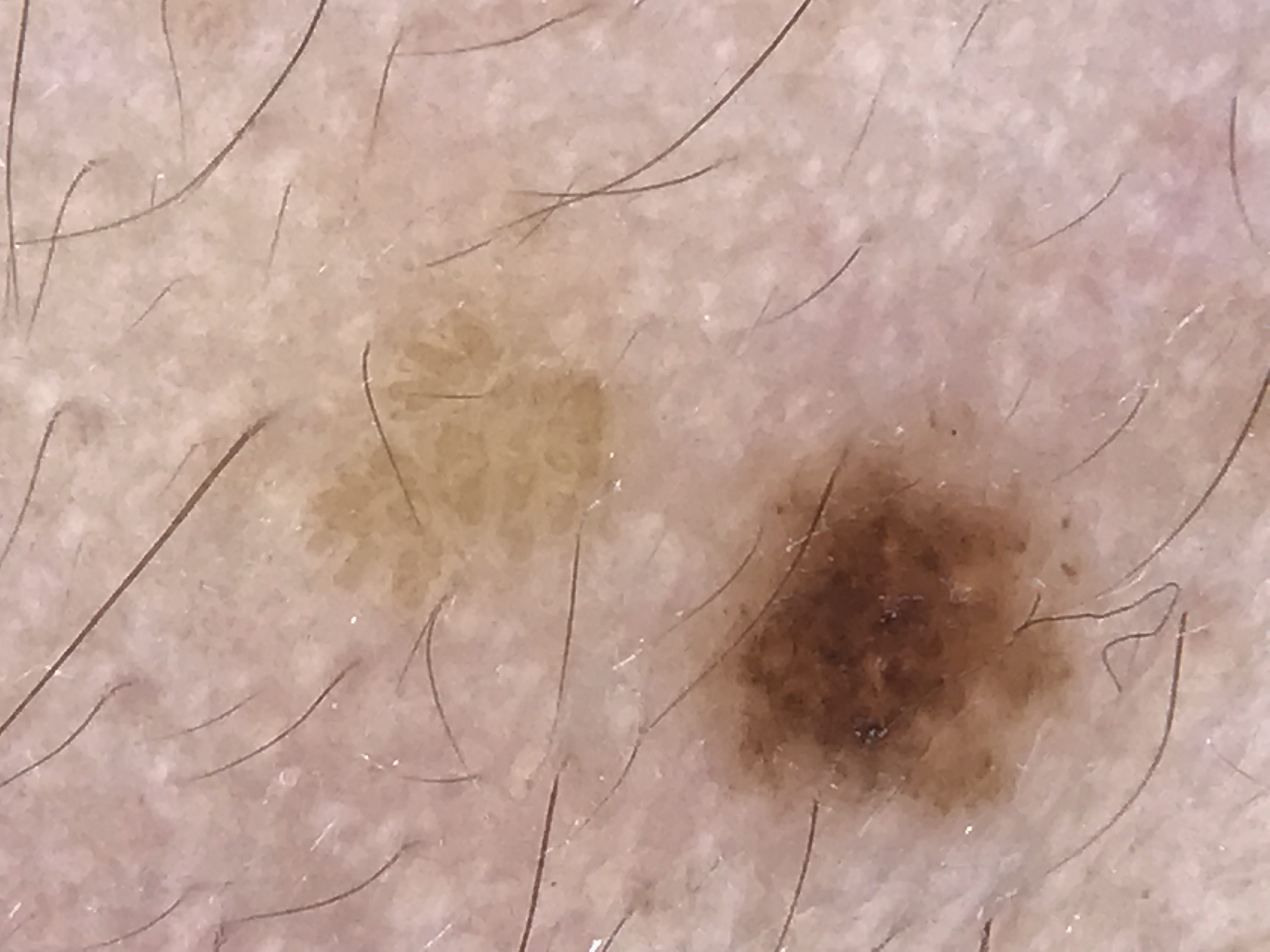Case:
• label · seborrheic keratosis (expert consensus)